The photograph is a close-up of the affected area. The lesion is associated with itching. Male subject, age 18–29. The back of the hand is involved:
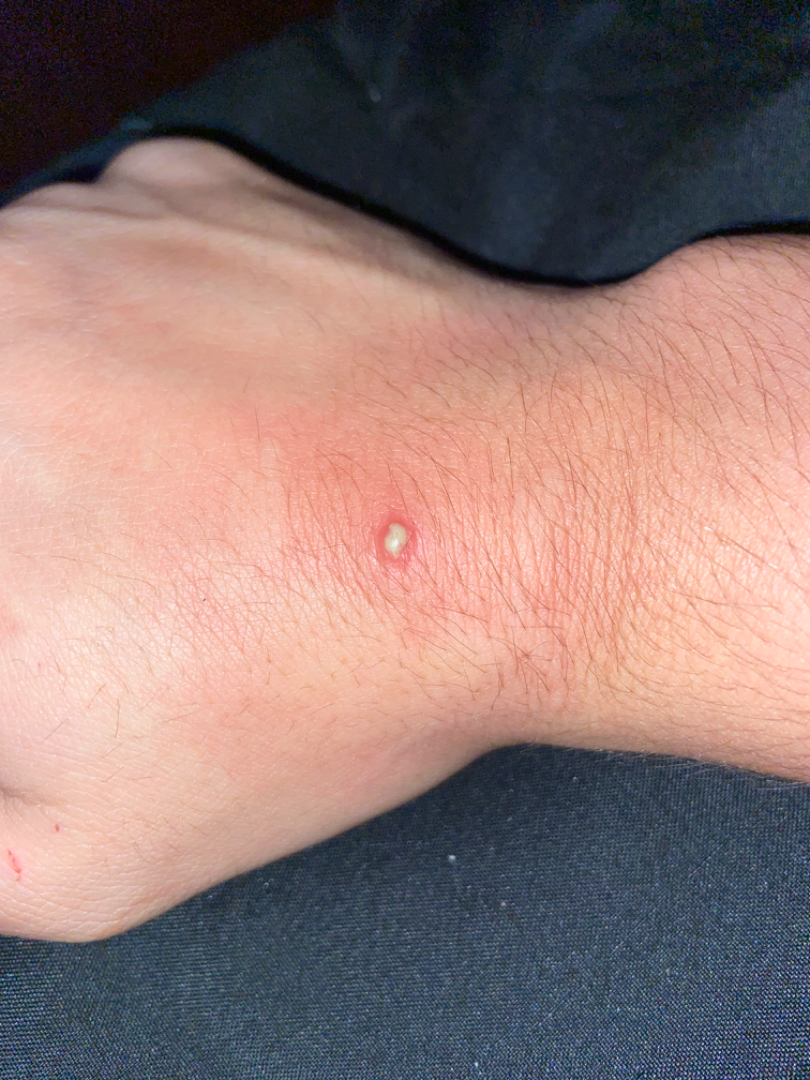On photographic review, Cellulitis (0.31); Insect Bite (0.31); Abscess (0.23); pustules (0.14).